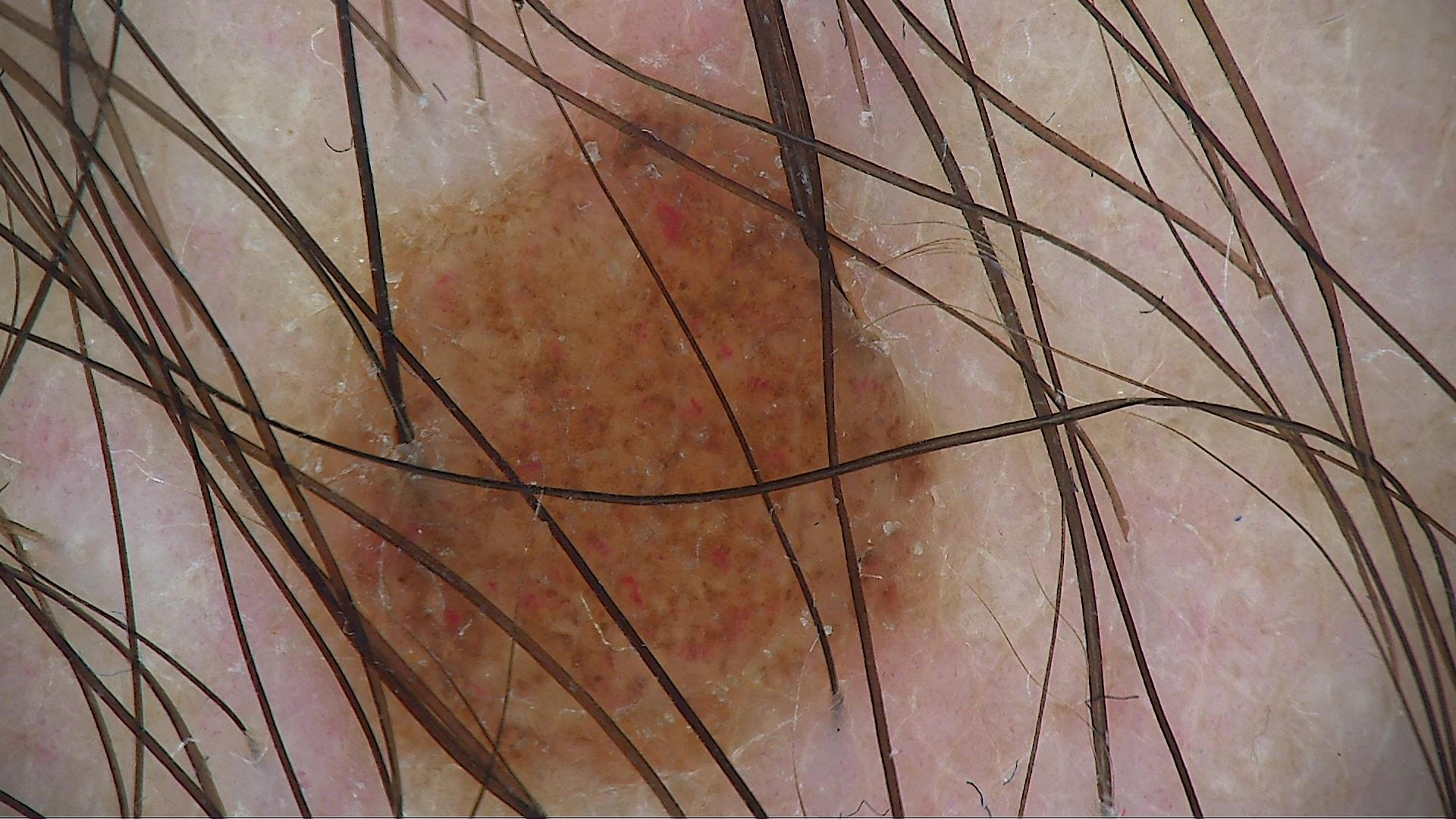Findings:
– imaging — dermatoscopy
– diagnosis — compound nevus (expert consensus)